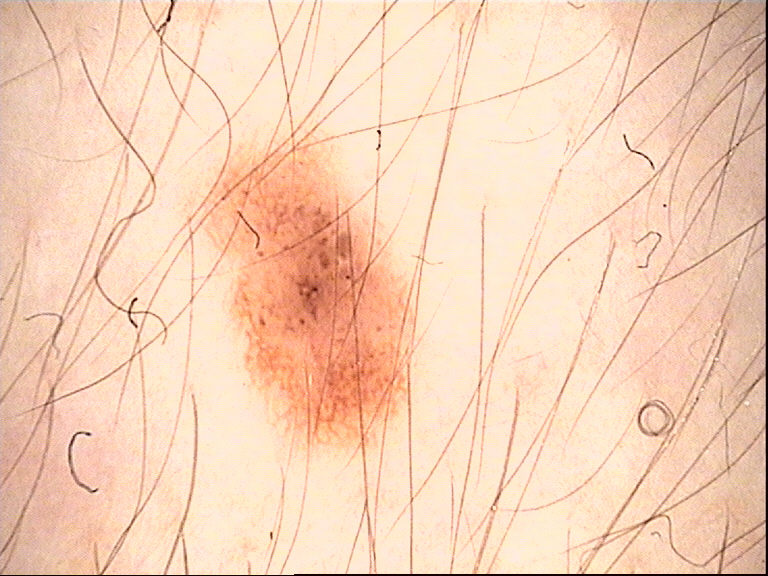The diagnosis was a dysplastic junctional nevus.